Close-up view, located on the arm — 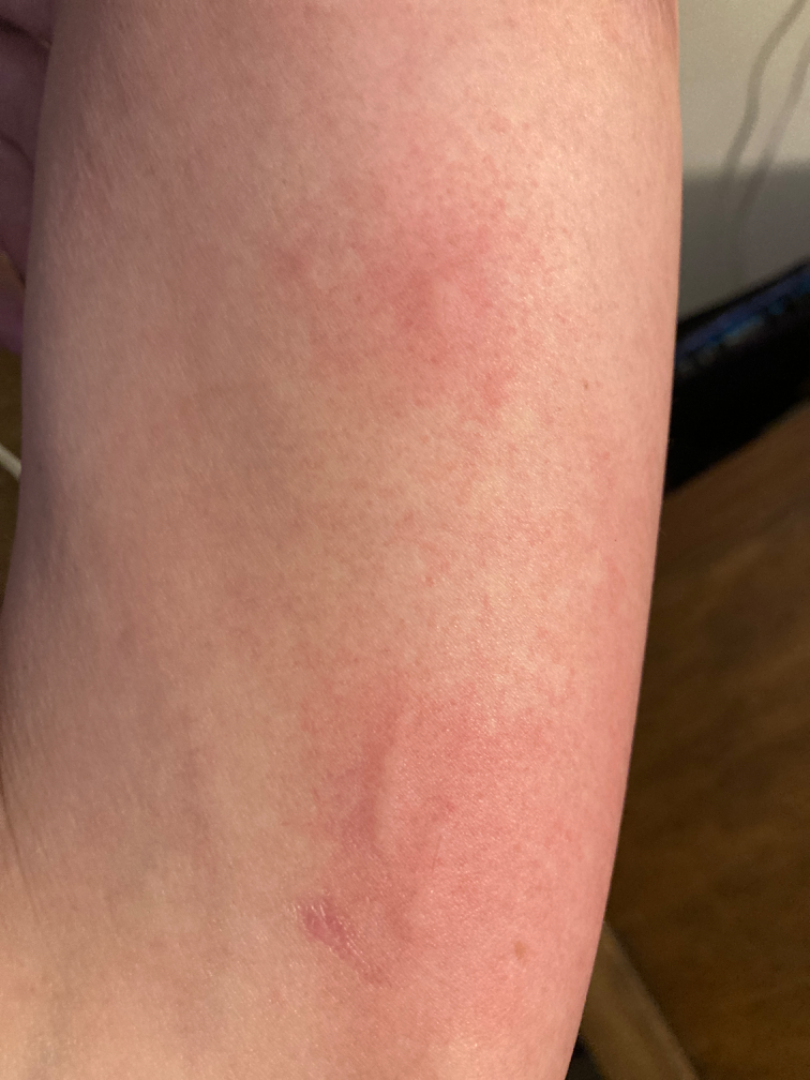<report>
<duration>about one day</duration>
<texture>raised or bumpy</texture>
<differential>
  <leading>Urticaria</leading>
</differential>
</report>